No associated systemic symptoms reported; the head or neck, back of the torso, leg and arm are involved; the contributor is 60–69, male; reported duration is less than one week; the contributor notes the lesion is raised or bumpy; the patient considered this skin that appeared healthy to them; the photograph was taken at an angle: 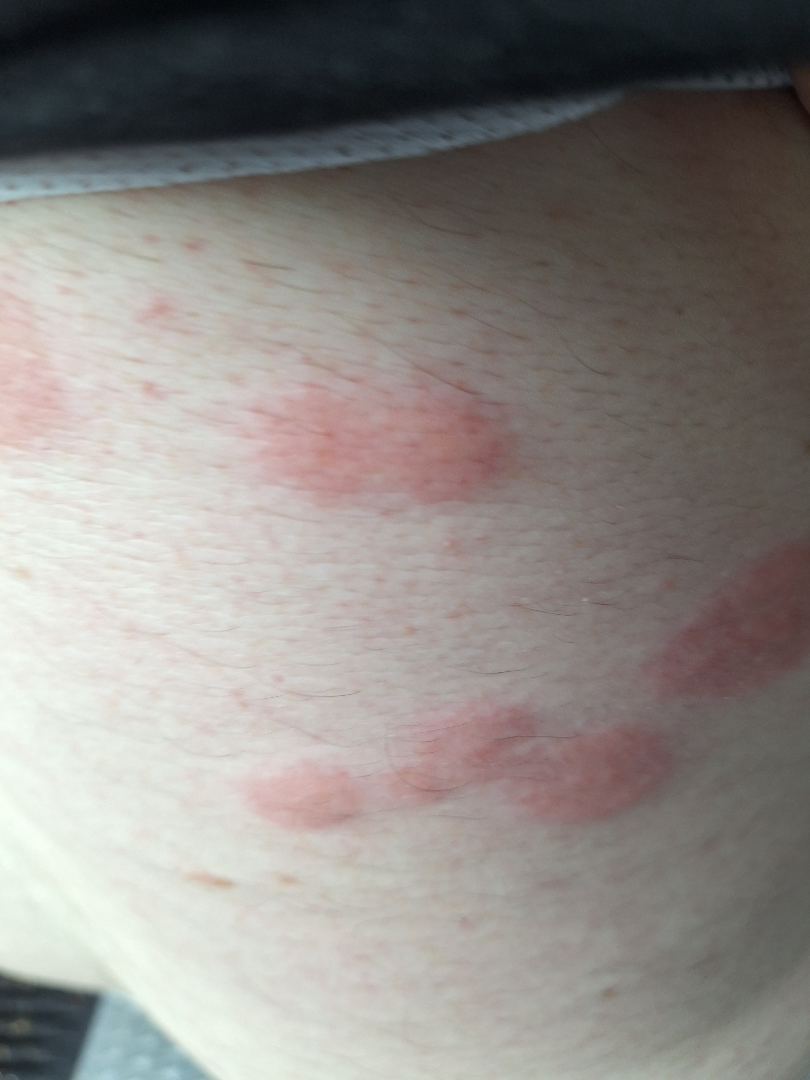On teledermatology review, Insect Bite (most likely).